A close-up photograph — 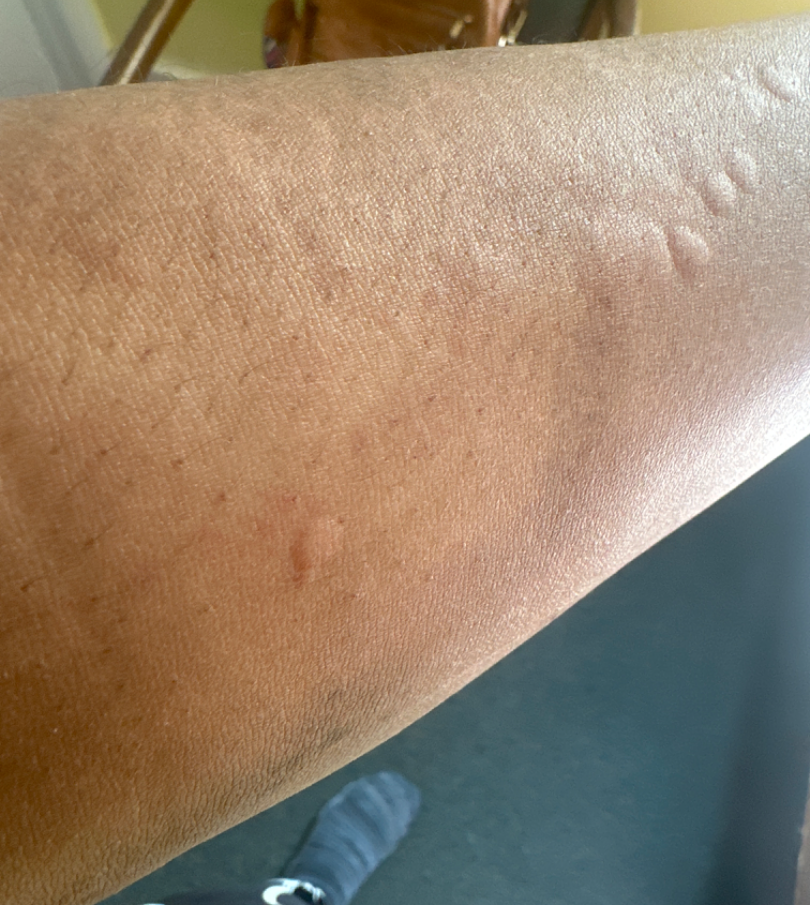On photographic review by a dermatologist, consistent with Urticaria.